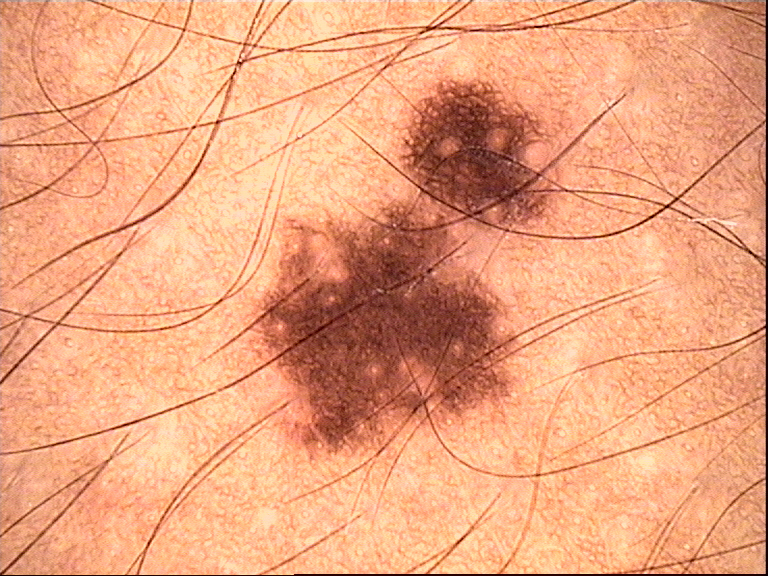{
  "diagnosis": {
    "name": "dysplastic junctional nevus",
    "code": "jd",
    "malignancy": "benign",
    "super_class": "melanocytic",
    "confirmation": "expert consensus"
  }
}